The chart notes prior skin cancer (patient or family), pesticide exposure, tobacco use, and alcohol use; the patient is Fitzpatrick I; a smartphone photograph of a skin lesion; a male patient age 60.
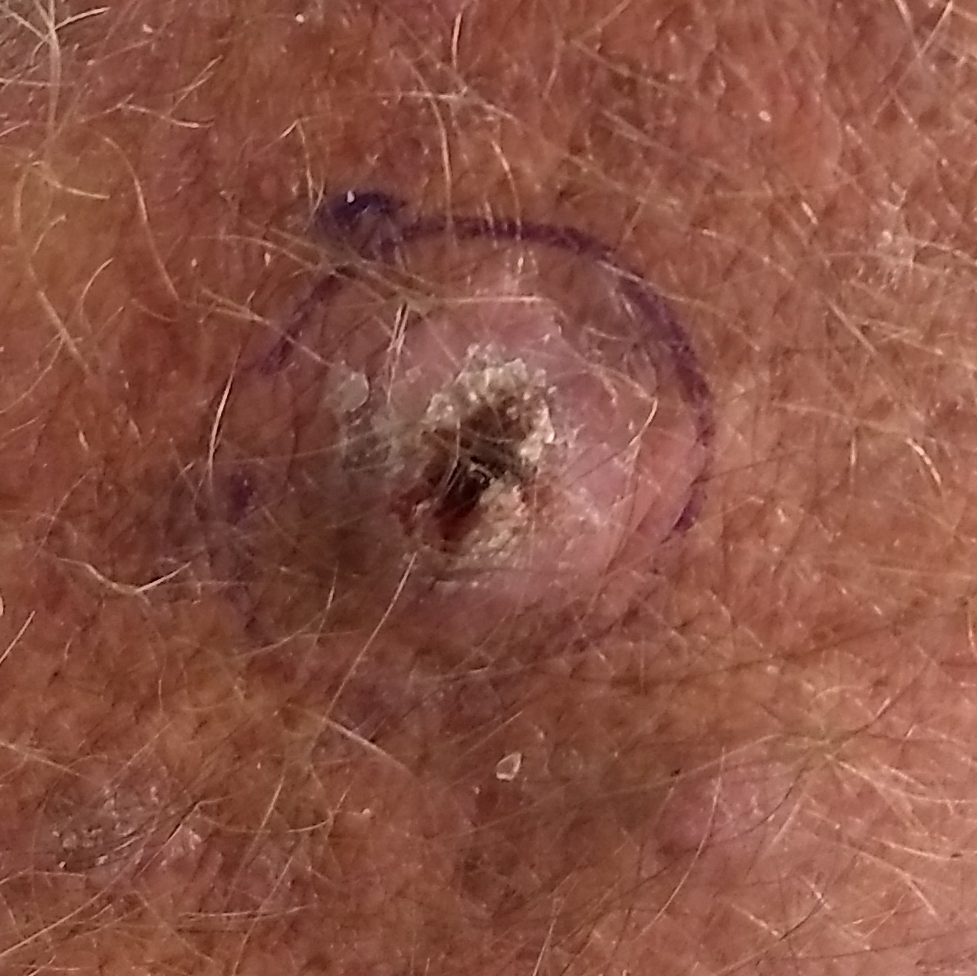The patient describes that the lesion is elevated, hurts, has bled, and itches.
Biopsy-confirmed as a skin cancer — a basal cell carcinoma.